Located on the arm, close-up view, reported lesion symptoms include enlargement and itching, the lesion is described as raised or bumpy, the contributor reports the condition has been present for less than one week: 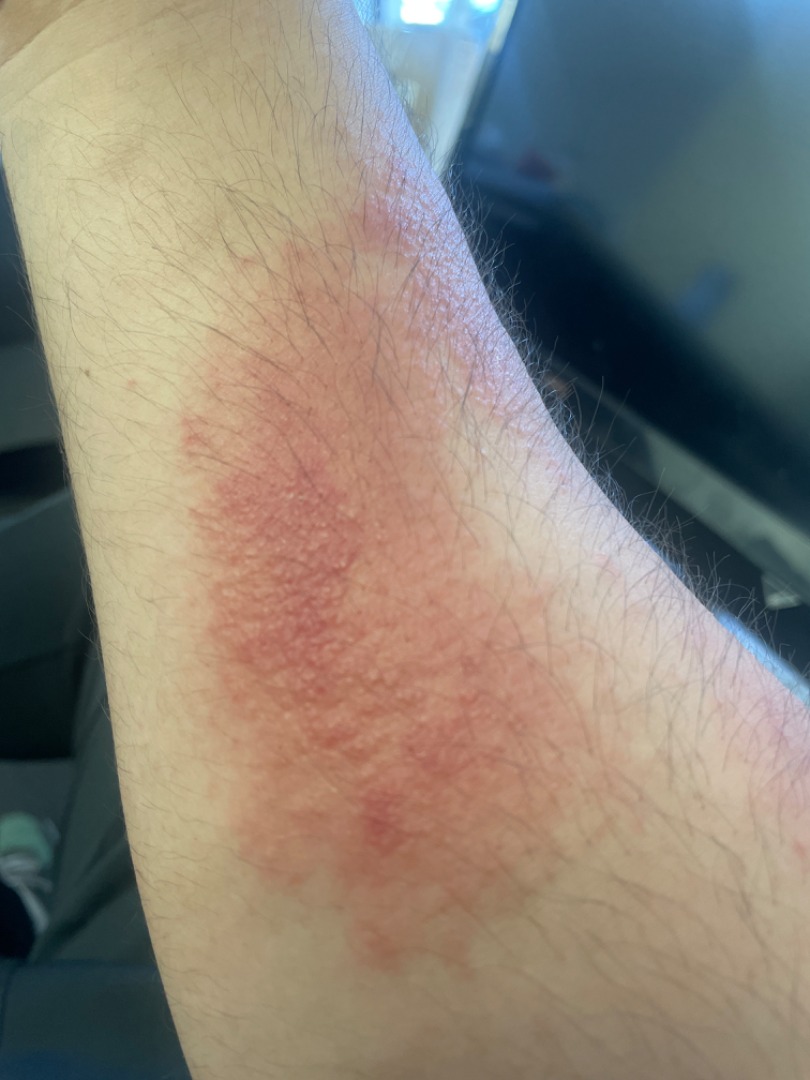assessment: the leading impression is Allergic Contact Dermatitis.